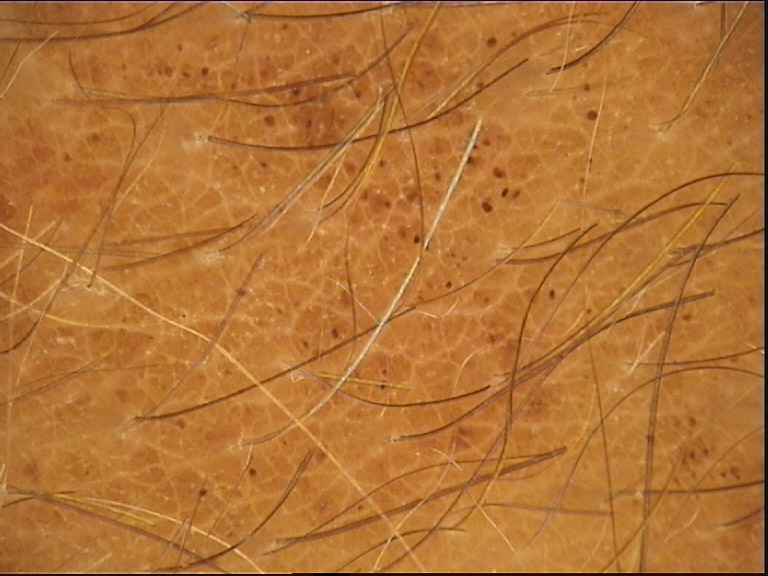Findings:
– image · dermoscopy
– lesion type · banal
– diagnostic label · congenital compound nevus (expert consensus)